A dermoscopic image of a skin lesion.
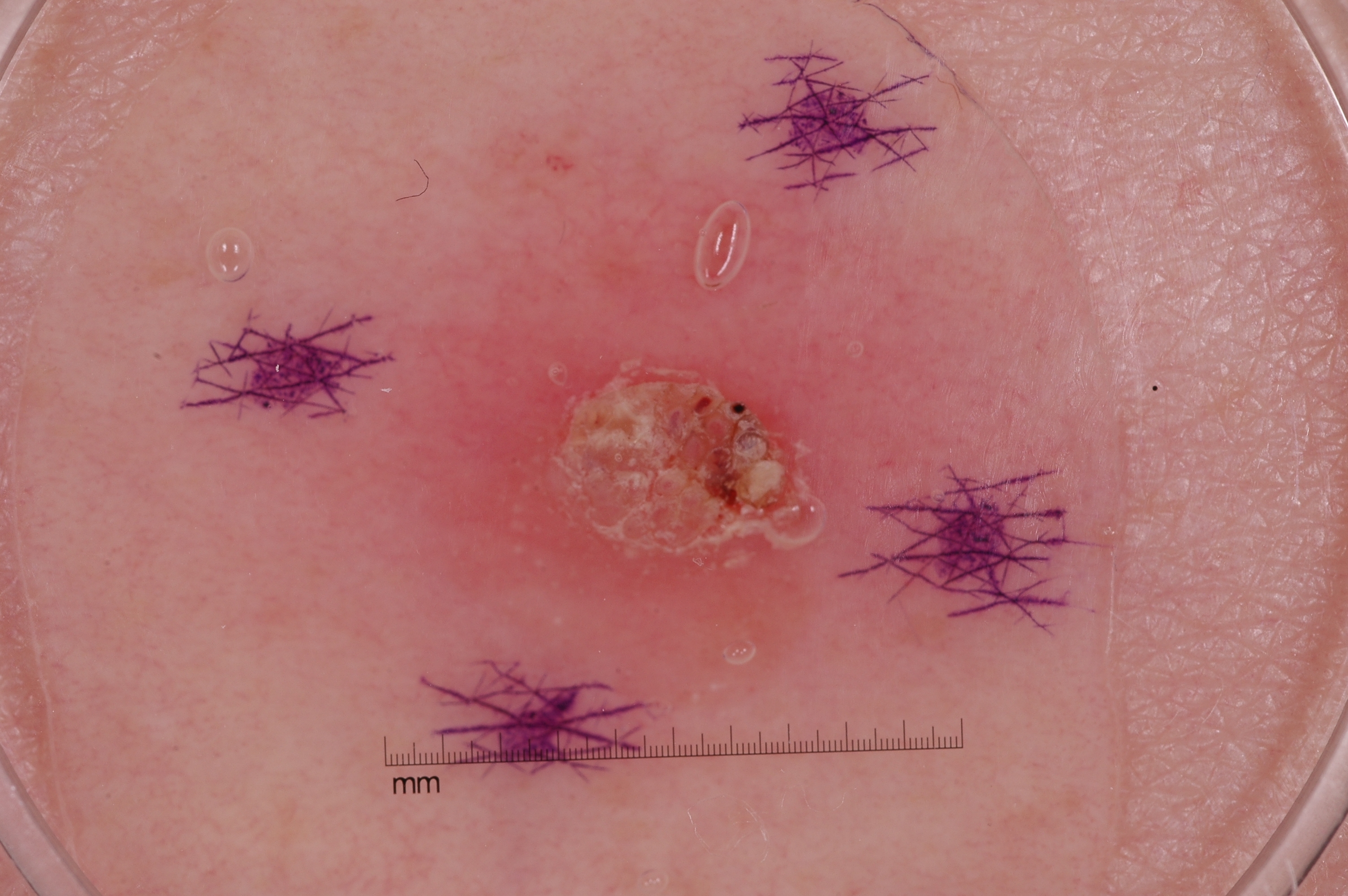Dermoscopic review identifies no negative network, pigment network, milia-like cysts, or streaks.
As (left, top, right, bottom), the lesion occupies the region [221, 98, 1106, 784].
A prominent lesion filling much of the field.
Diagnosed as a seborrheic keratosis.